A dermoscopy image of a single skin lesion: 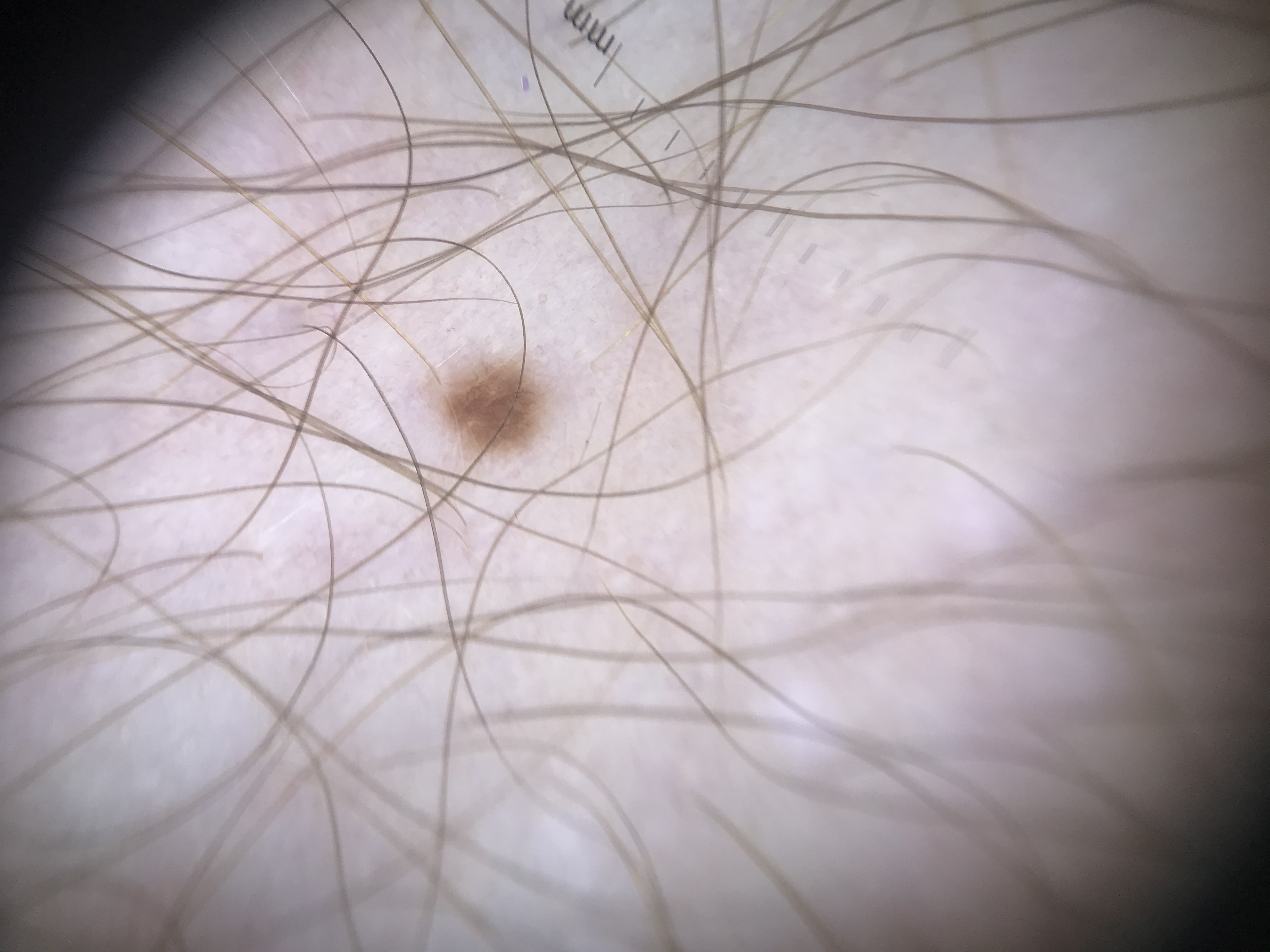Q: What is the diagnosis?
A: junctional nevus (expert consensus)